The patient described the issue as a rash. Located on the back of the hand. The photo was captured at a distance. The patient is a female aged 18–29 — 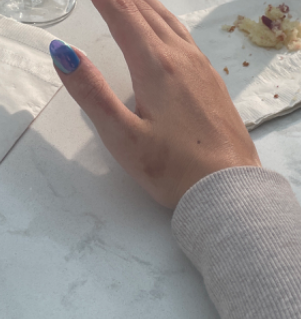Impression: One reviewing dermatologist: the leading consideration is Photodermatitis; also raised was Hyperpigmentation disorder; an alternative is Post-Inflammatory hyperpigmentation.